Male patient, age 60–69 · texture is reported as raised or bumpy · the patient considered this a rash · the lesion involves the front of the torso · the lesion is associated with burning · the photograph is a close-up of the affected area · present for less than one week · no constitutional symptoms were reported — 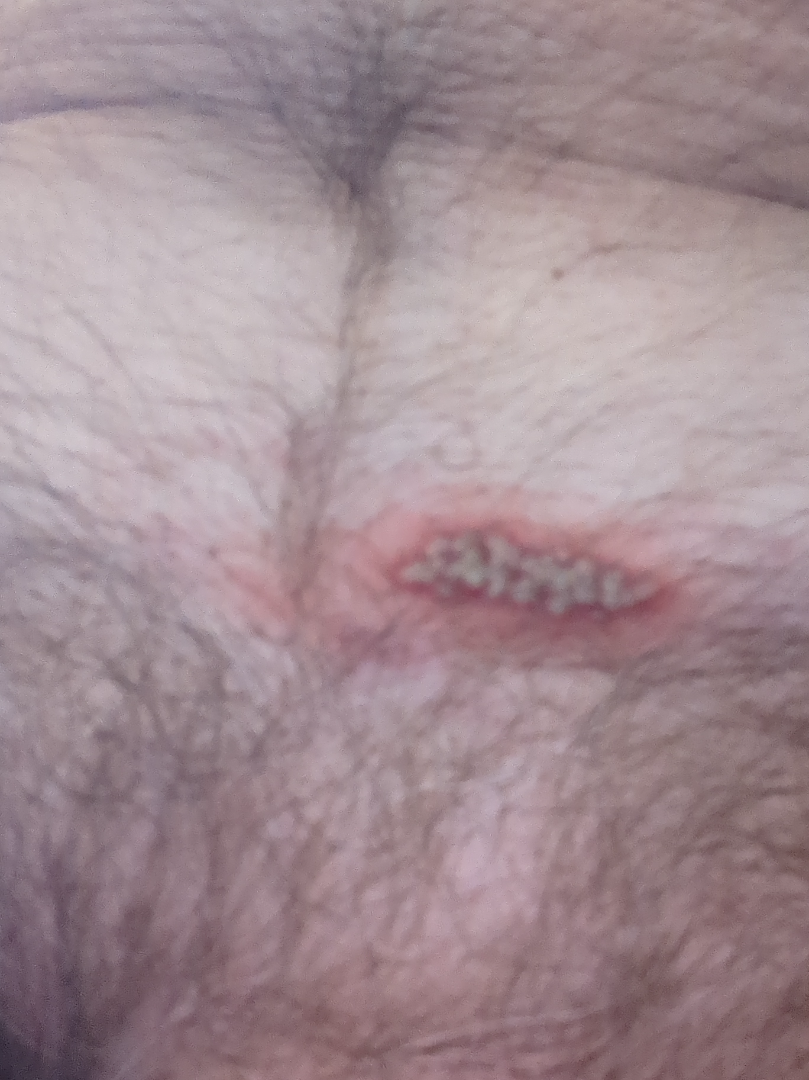differential:
  leading:
    - Herpes Simplex
  considered:
    - Herpes Zoster